The patient is a male aged around 60; dermoscopy of a skin lesion — 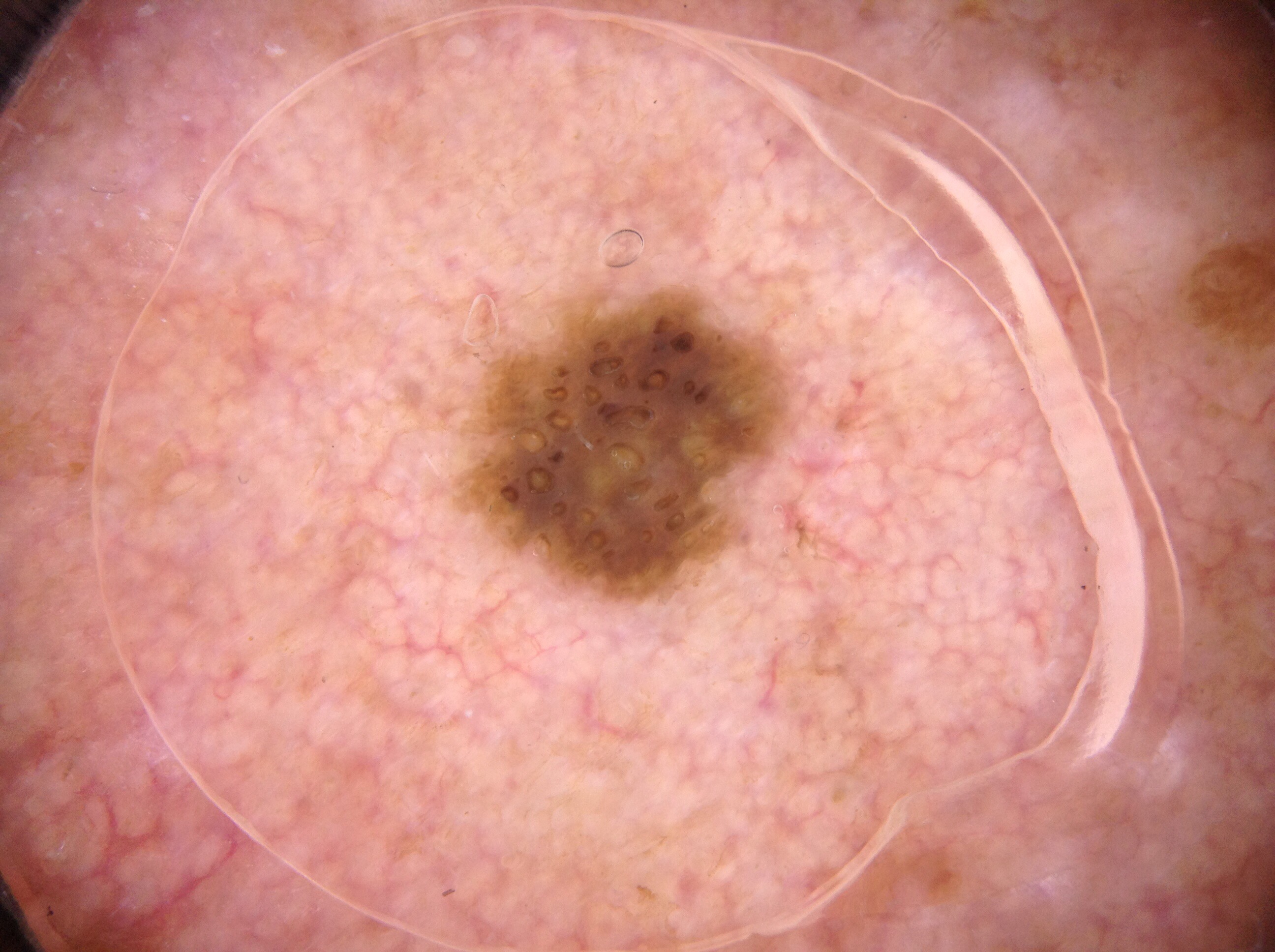As (left, top, right, bottom), the lesion is bounded by 468 297 777 595. Dermoscopic examination shows no negative network, milia-like cysts, pigment network, or streaks. The clinical diagnosis was a seborrheic keratosis.